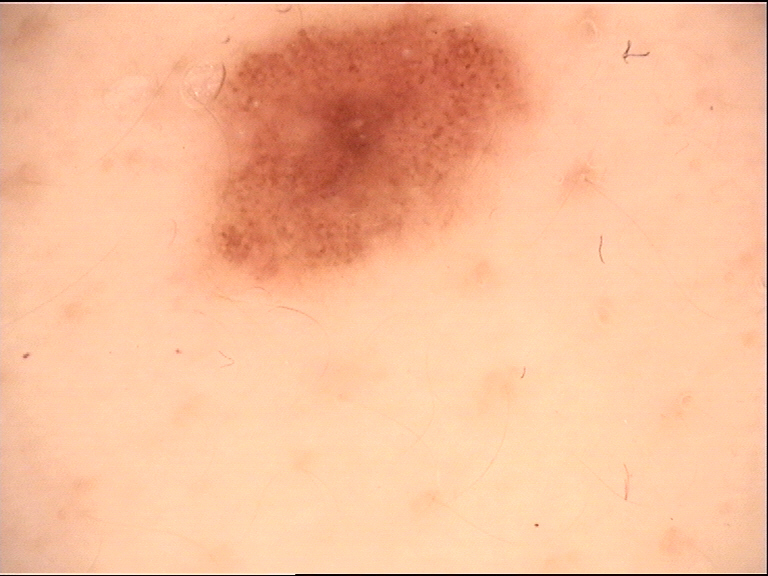Diagnosed as a benign lesion — a dysplastic compound nevus.